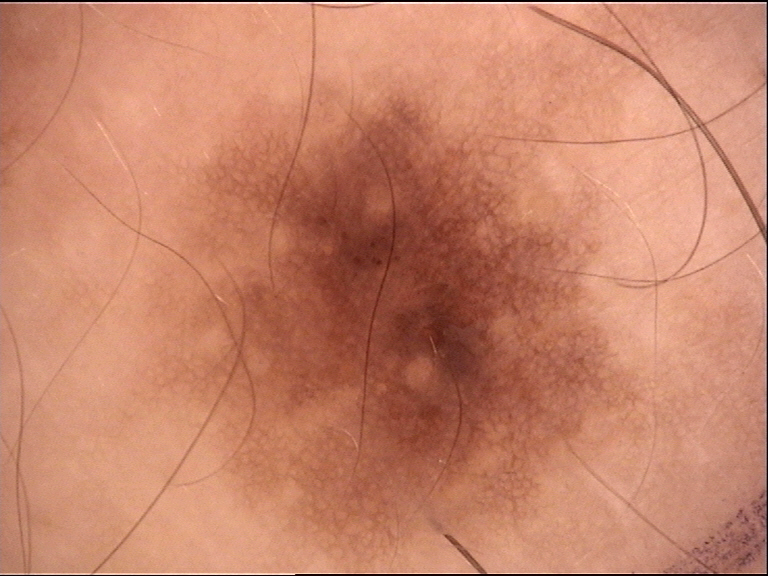assessment: dysplastic junctional nevus (expert consensus)